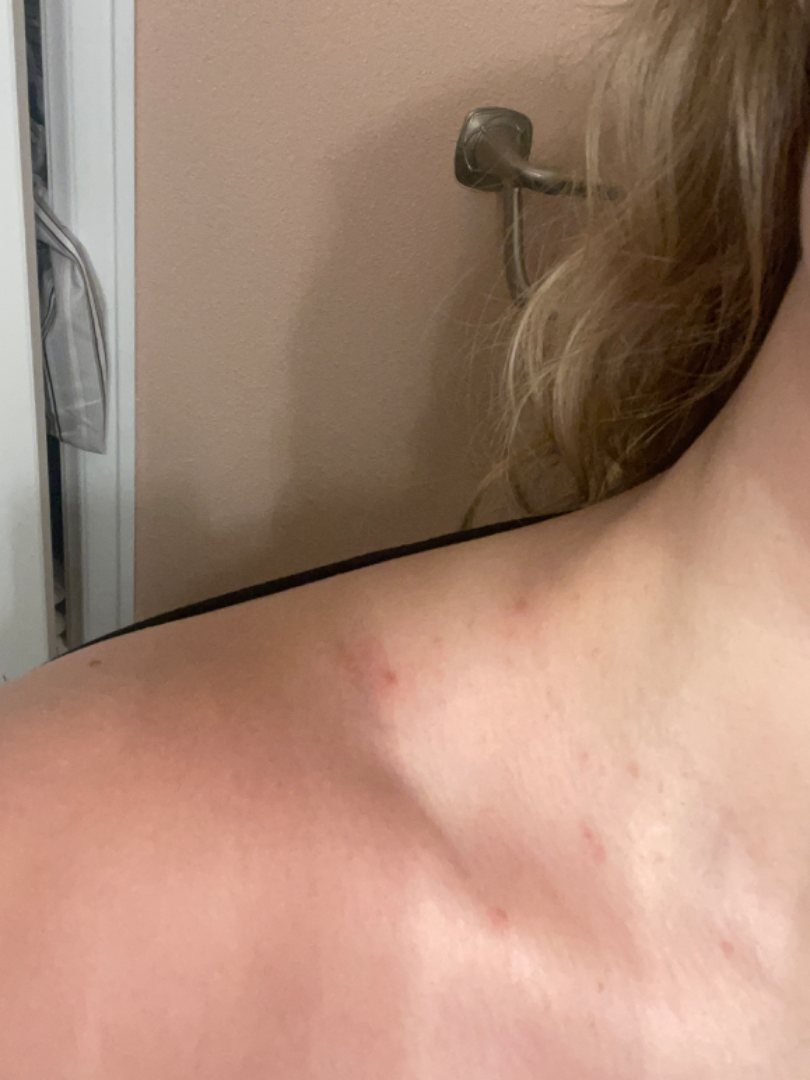Findings:
The condition could not be reliably identified from the image.